Female patient, age 50–59 · this is a close-up image · located on the leg:
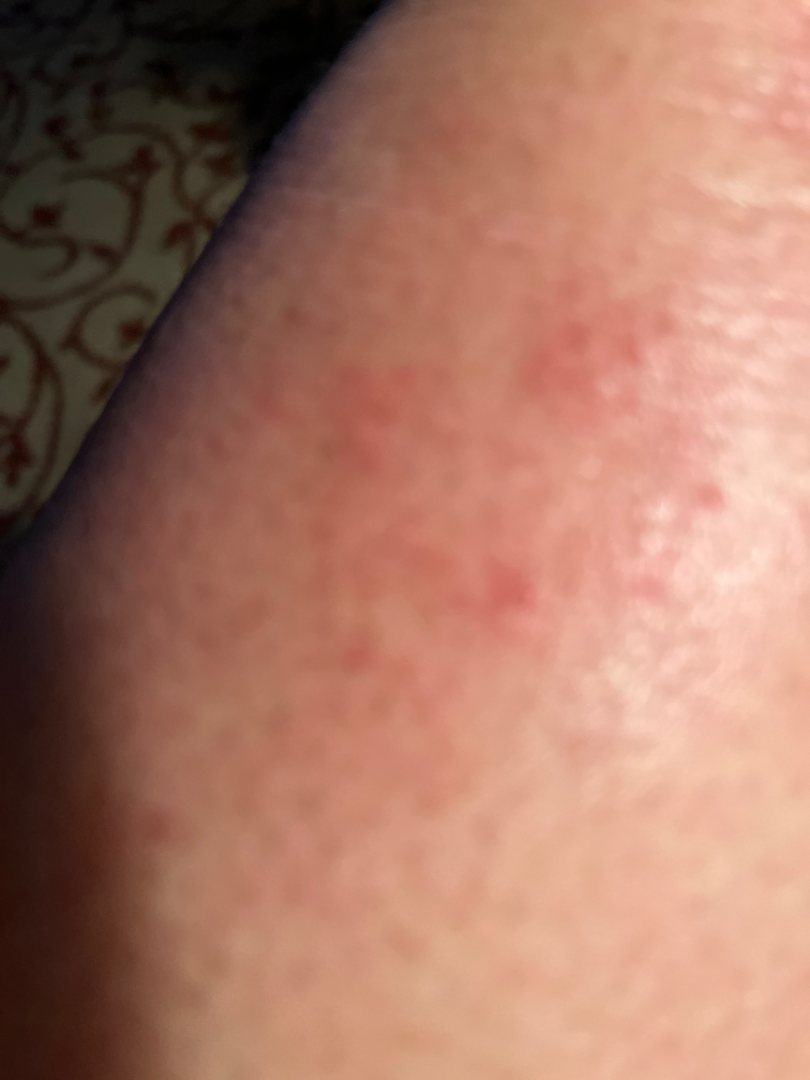described texture: raised or bumpy
patient-reported symptoms: itching
patient's own categorization: a rash
history: more than one year
impression: in keeping with Eczema